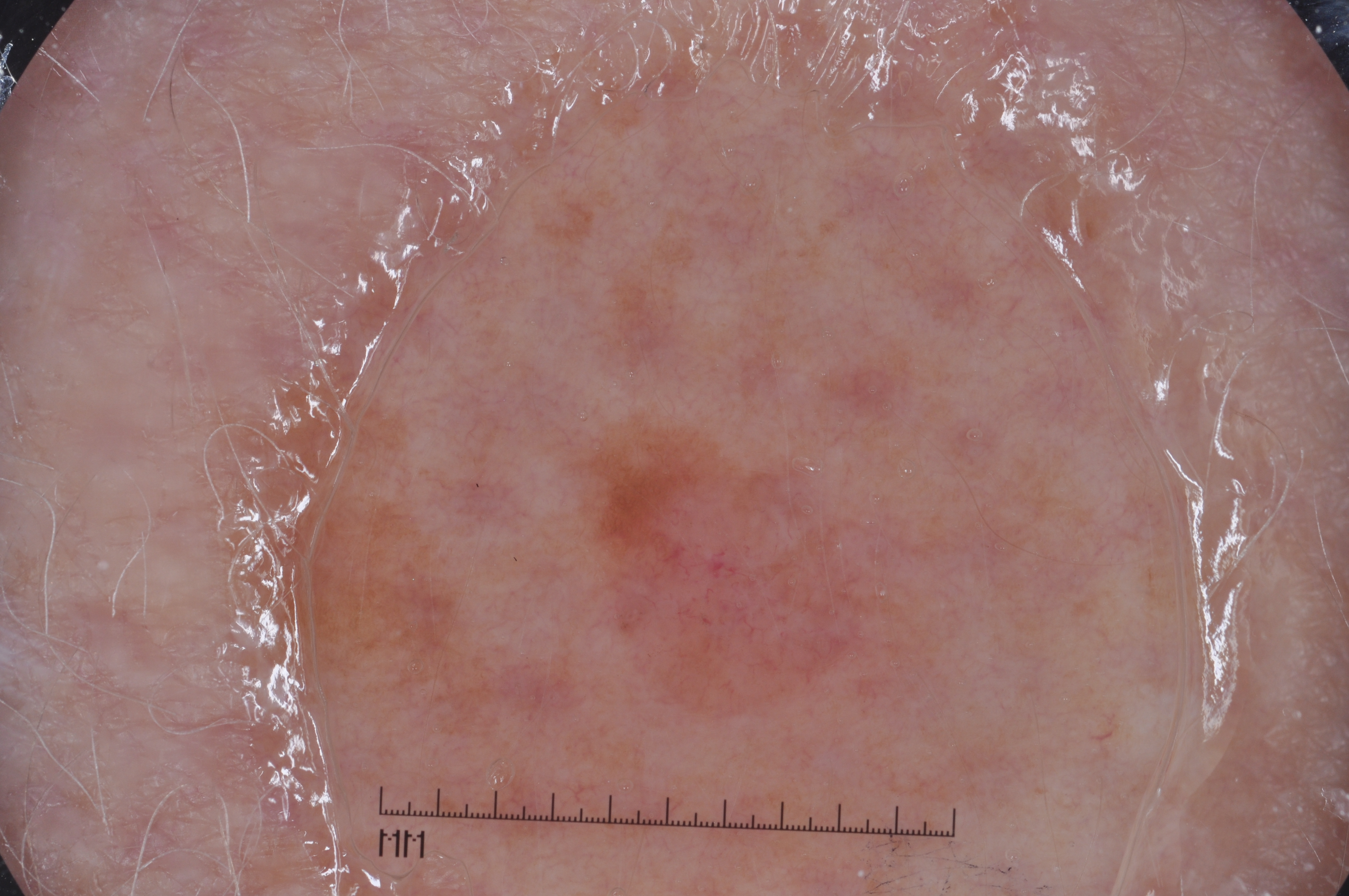A dermoscopic close-up of a skin lesion.
In (x1, y1, x2, y2) order, the lesion is located at [567, 397, 891, 735].
Confirmed on histopathology as a melanoma, a malignant lesion.